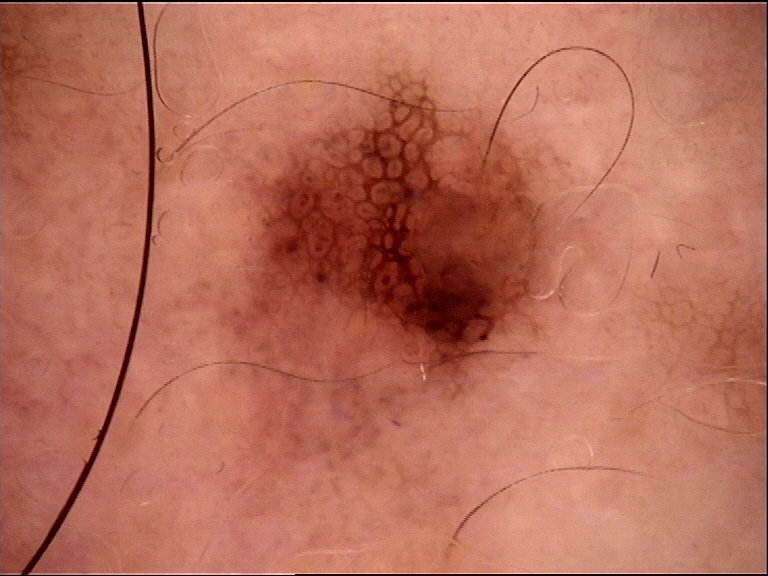Diagnosed as a dysplastic junctional nevus.